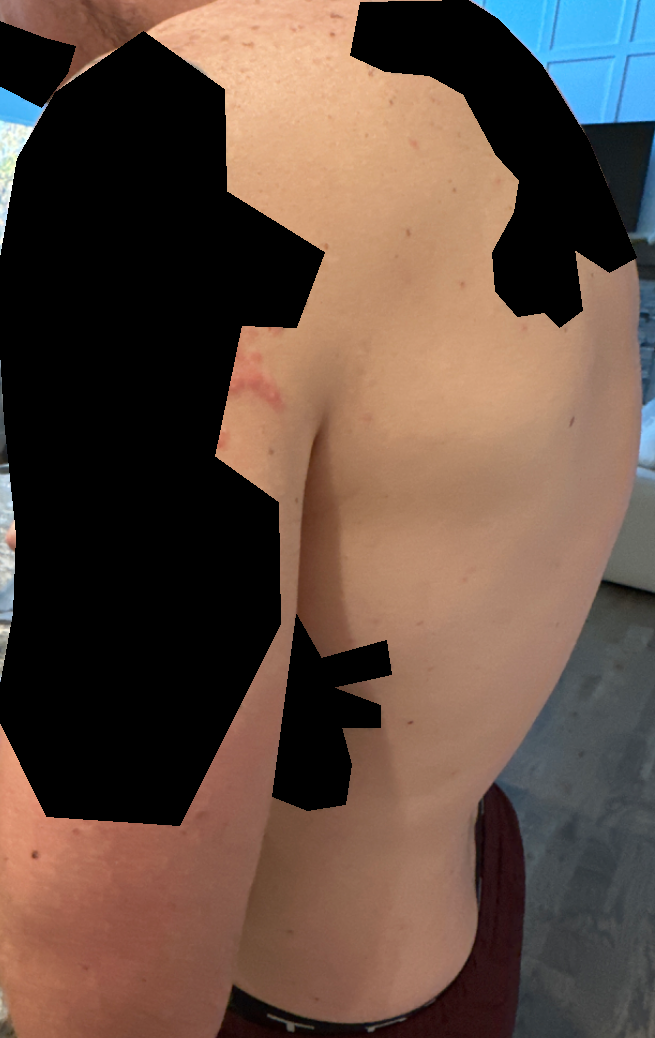Diagnostic features were not clearly distinguishable in this photograph. The photo was captured at a distance. The patient indicates bothersome appearance. The condition has been present for less than one week. The lesion involves the arm. The patient indicates the lesion is raised or bumpy.